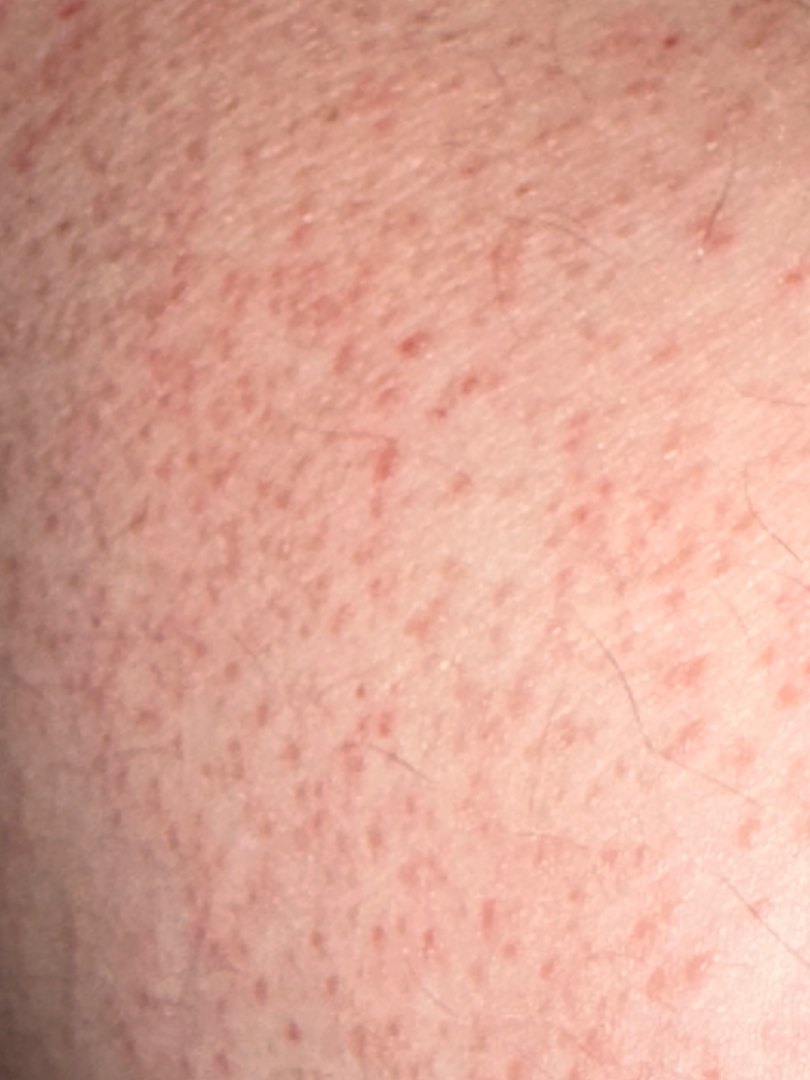The case was indeterminate on photographic review.